The contributor is 18–29, male. The photograph was taken at an angle. Located on the head or neck.
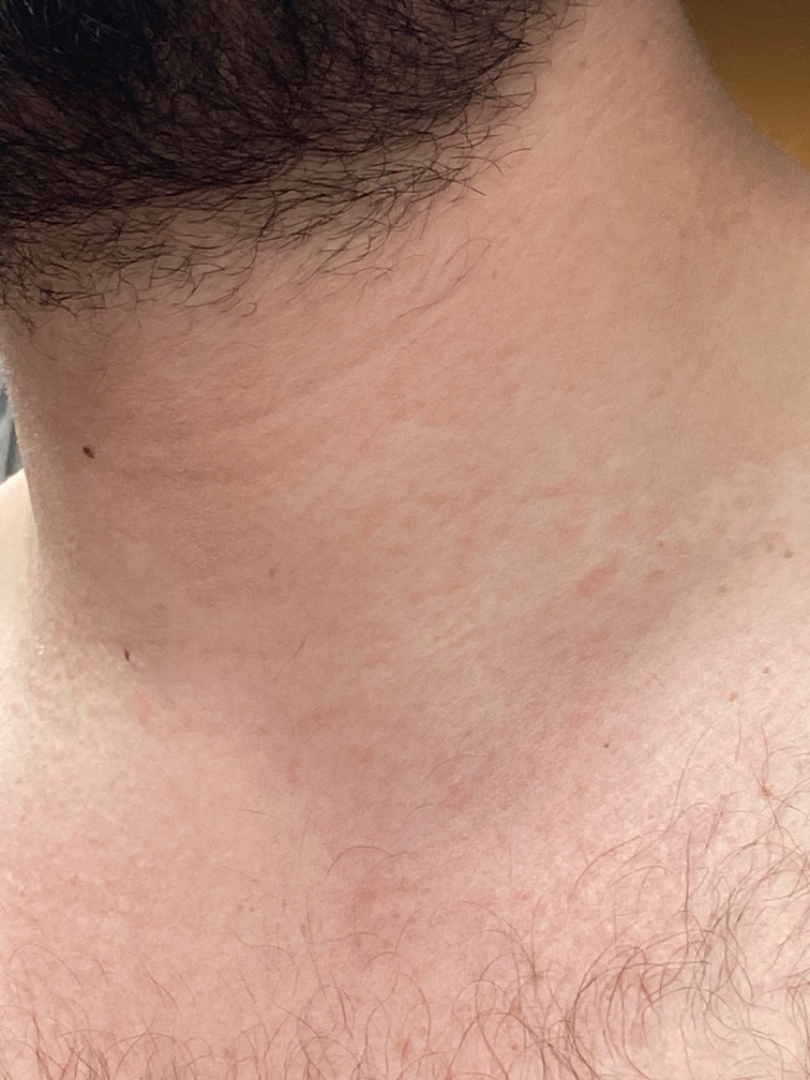The case was indeterminate on photographic review. Present for more than one year. The patient considered this a rash. Texture is reported as rough or flaky.